The photograph is a close-up of the affected area · located on the back of the torso:
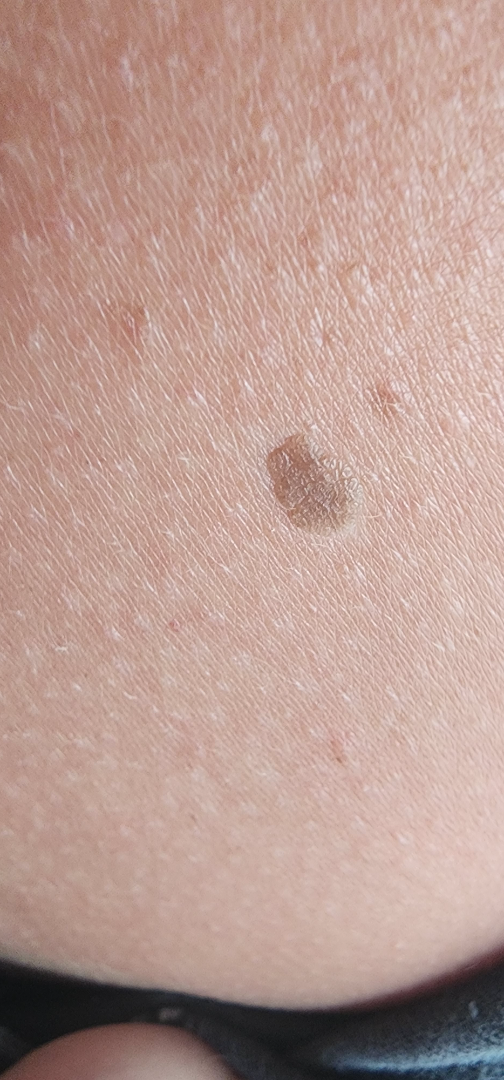Q: Texture?
A: raised or bumpy
Q: Any systemic symptoms?
A: none reported
Q: What symptoms does the patient report?
A: bothersome appearance
Q: What is the dermatologist's impression?
A: the primary impression is SK/ISK; with consideration of Melanocytic Nevus; less likely is Actinic Keratosis